A dermatoscopic image of a skin lesion.
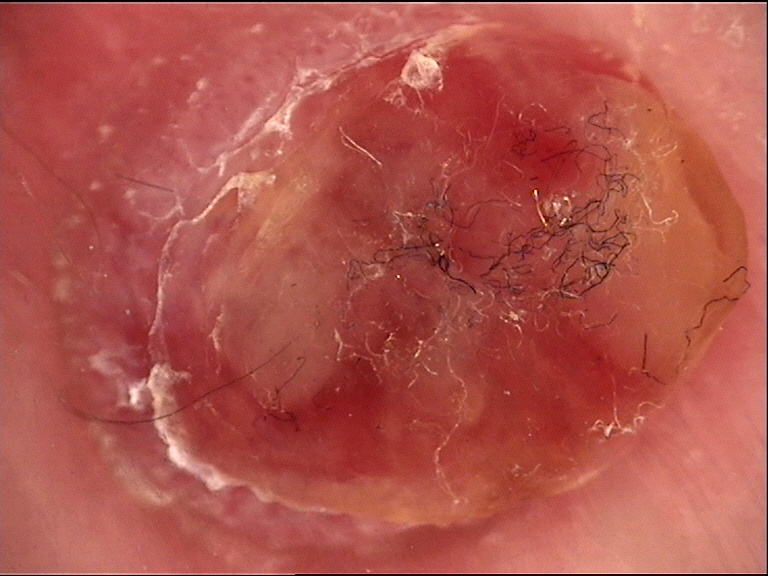Case:
* lesion type: vascular
* diagnosis: Kaposi sarcoma (biopsy-proven)